Female contributor, age 18–29. The lesion involves the top or side of the foot and leg. An image taken at an angle: 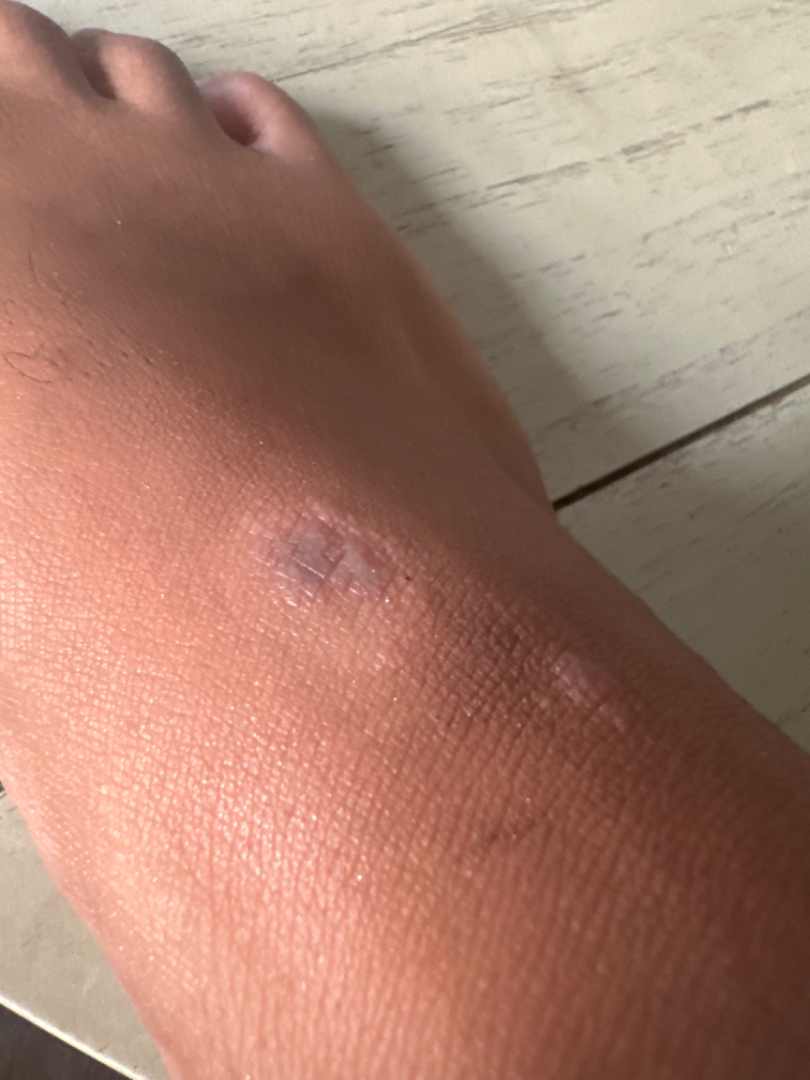Lichen planus/lichenoid eruption, Lichen Simplex Chronicus and Insect Bite were considered with similar weight.